The leg, arm and top or side of the foot are involved; close-up view:
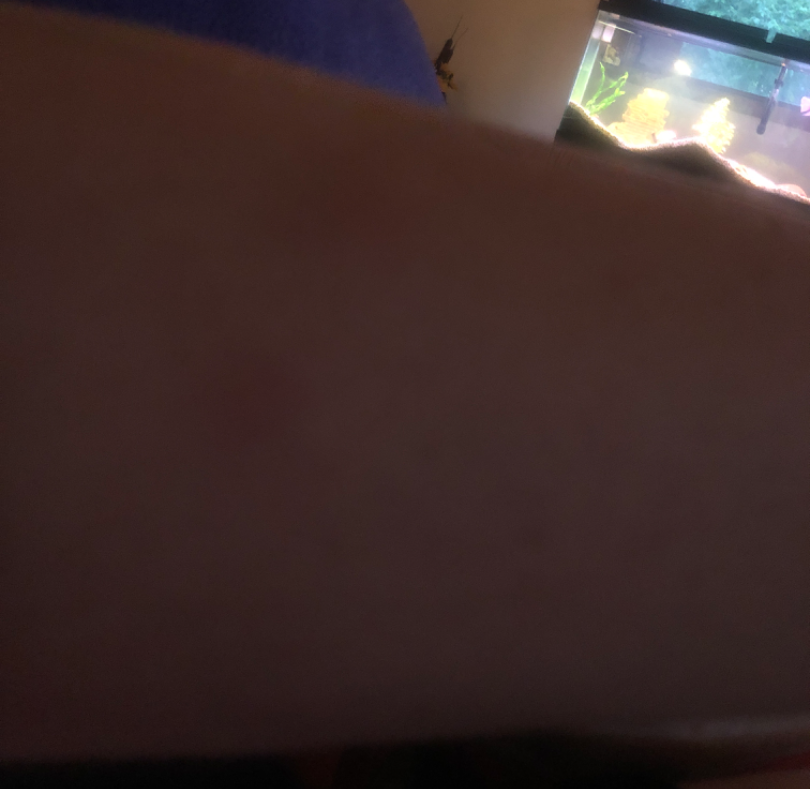The case was difficult to assess from the available photograph.